Close-up view, Fitzpatrick skin type IV; non-clinician graders estimated Monk skin tone scale 2 or 3, present for about one day, the patient reported no systemic symptoms, located on the leg, the lesion is described as flat:
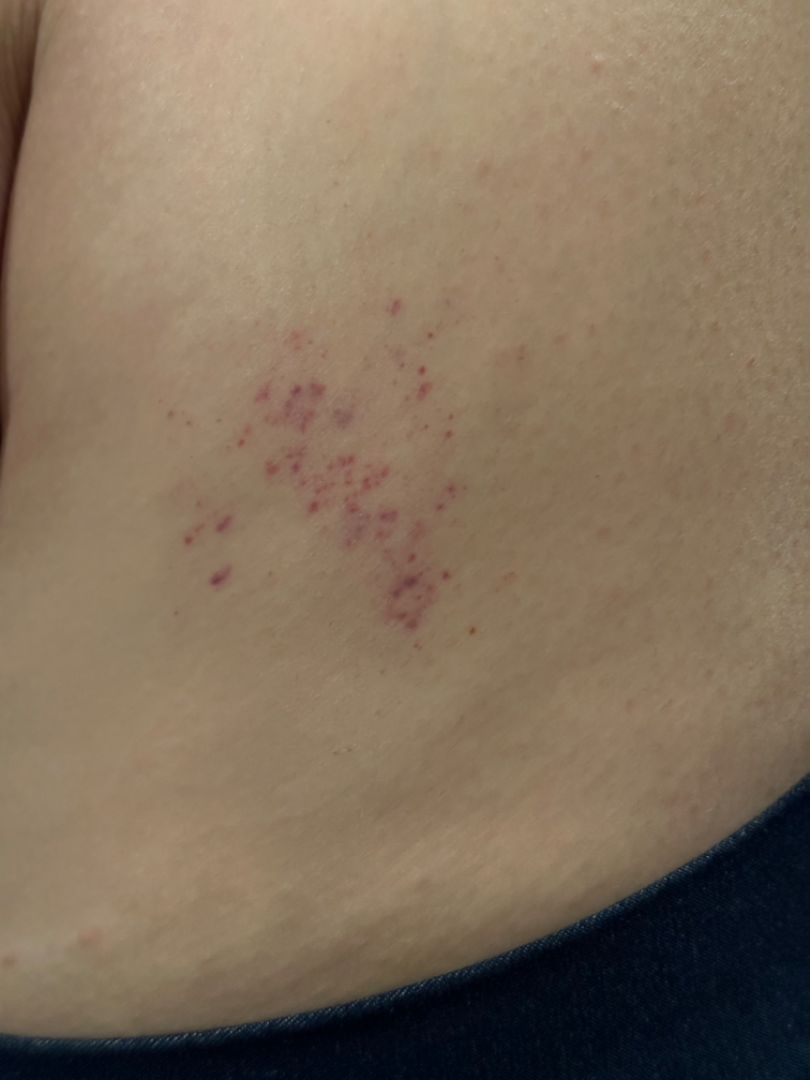differential diagnosis: consistent with Purpura.